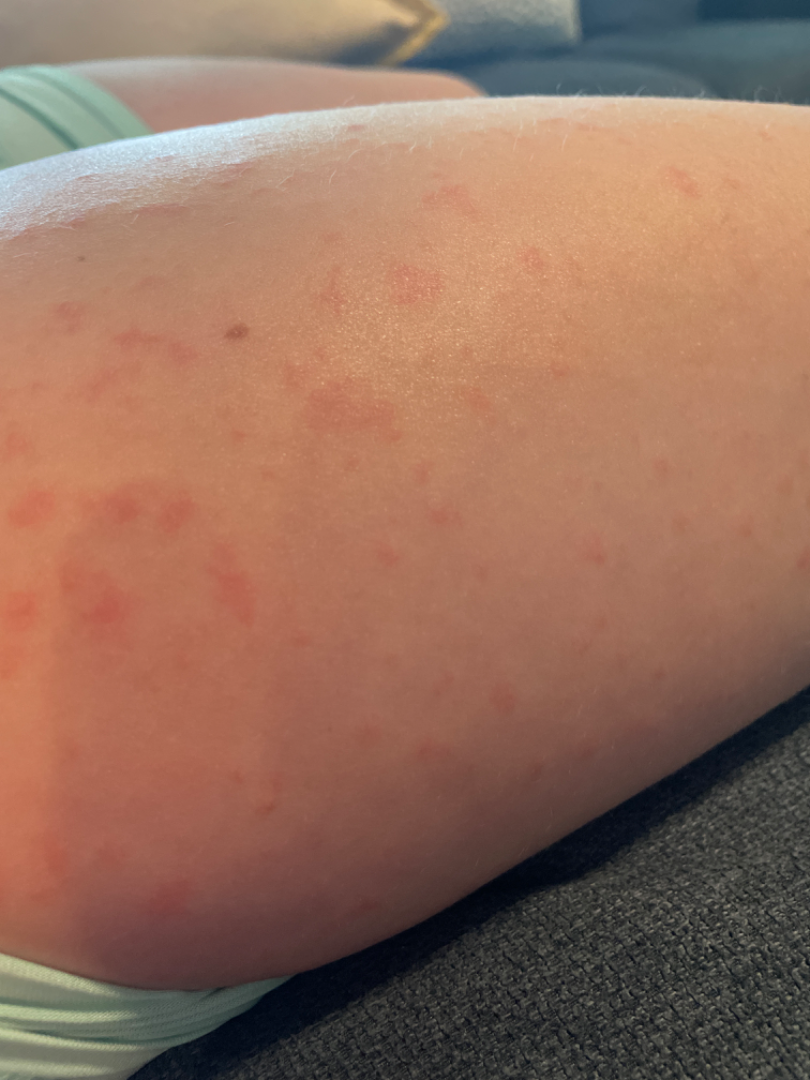described texture = flat
patient describes the issue as = a rash
onset = about one day
subject = female, age 18–29
body site = leg
image framing = at an angle
symptoms = none reported
assessment = most consistent with Viral Exanthem; the differential also includes Drug Rash; less probable is Urticaria; a more distant consideration is Eczema